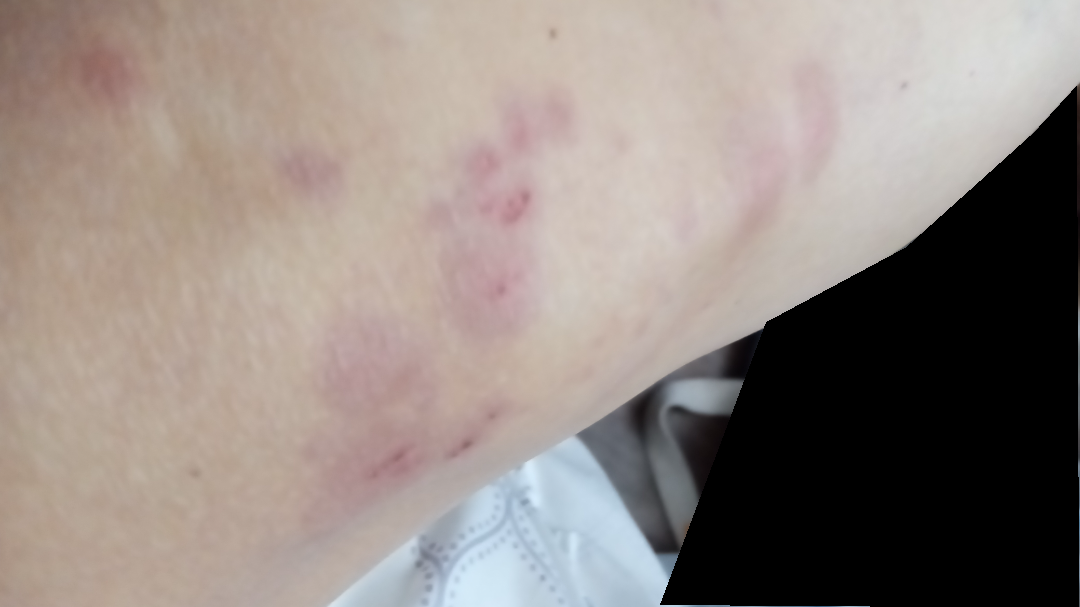Q: Could the case be diagnosed?
A: not assessable
Q: Reported symptoms?
A: enlargement, itching and pain
Q: When did this start?
A: one to four weeks
Q: What is the framing?
A: close-up
Q: Who is the patient?
A: female, age 60–69
Q: How does the patient describe it?
A: a rash
Q: Constitutional symptoms?
A: none reported
Q: Texture?
A: raised or bumpy
Q: Anatomic location?
A: top or side of the foot, leg and front of the torso